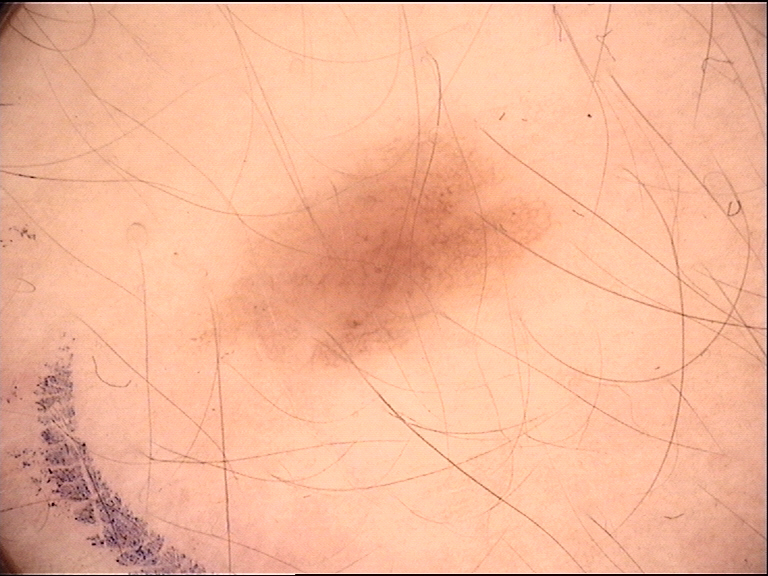Conclusion:
Classified as a dysplastic junctional nevus.